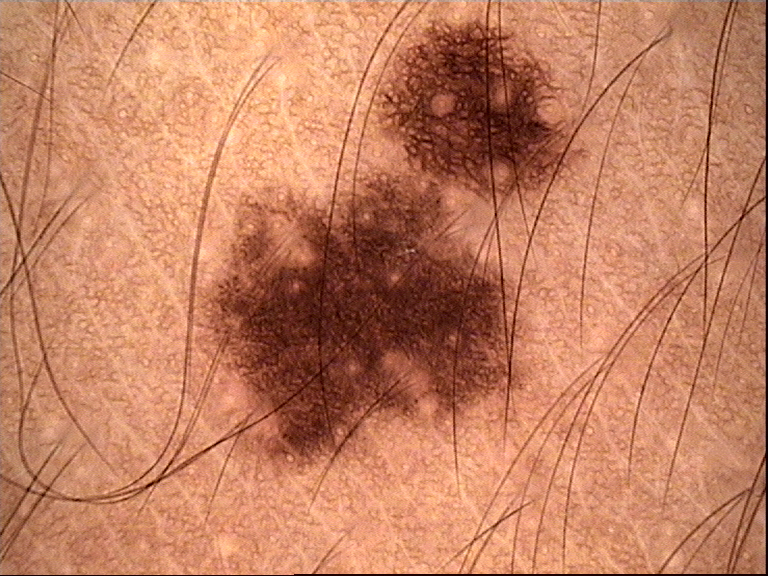label — dysplastic junctional nevus (expert consensus).